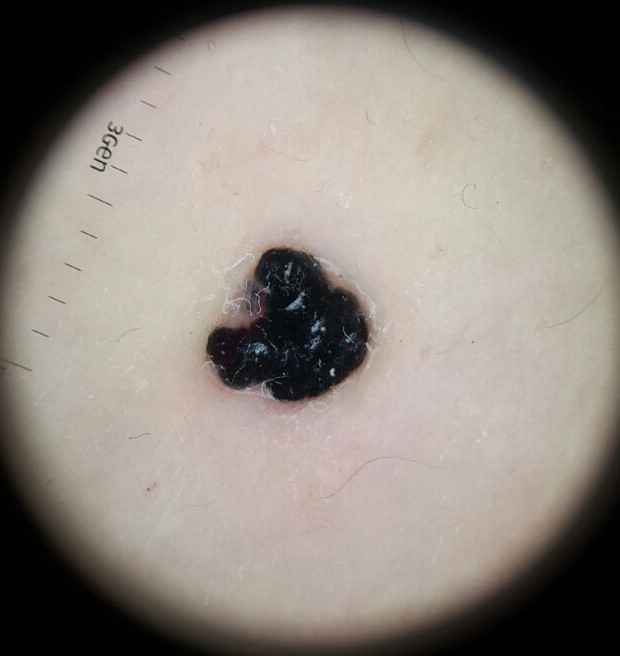image type — dermatoscopy; class — angiokeratoma (expert consensus).